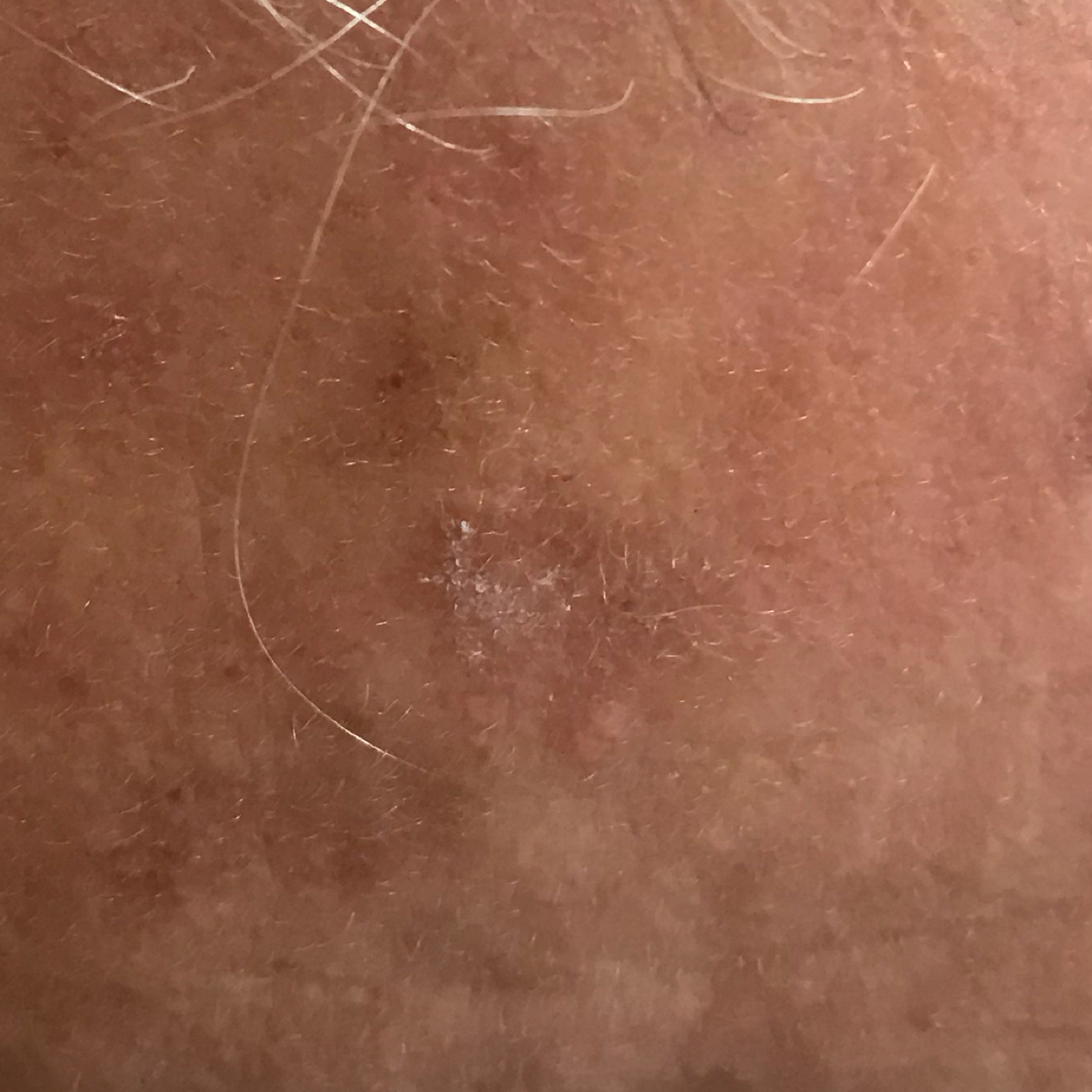Notes:
- location · the face
- assessment · actinic keratosis (clinical consensus)